The patient indicates the condition has been present for about one day · the subject is 18–29, female · the patient indicates itching · this is a close-up image · texture is reported as raised or bumpy and fluid-filled:
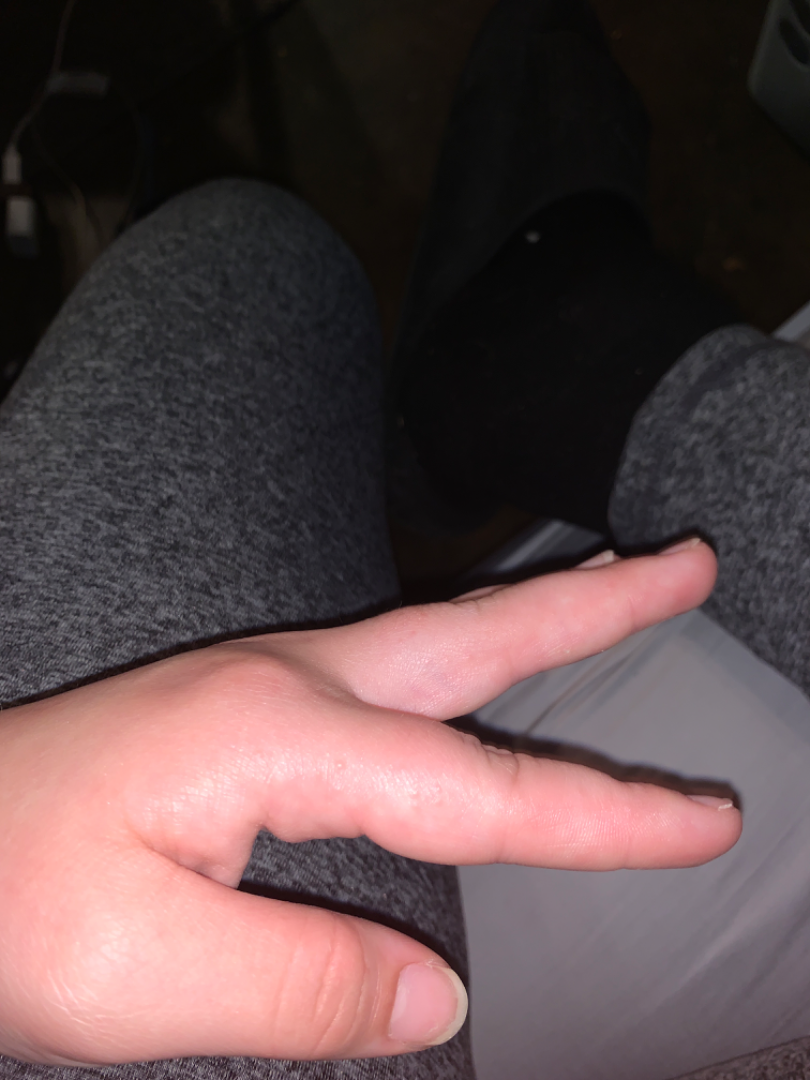  differential:
    leading:
      - Eczema
    unlikely:
      - Scabies
      - Hypersensitivity